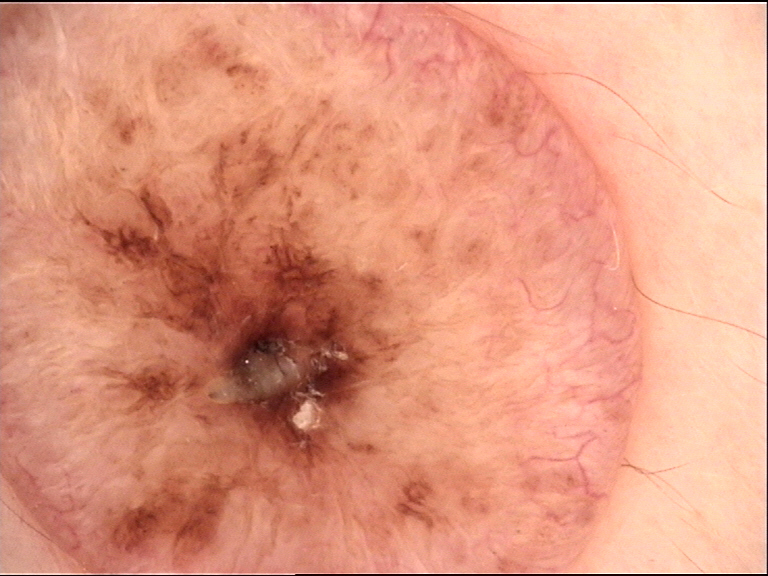modality = dermatoscopy; diagnosis = dermal nevus (expert consensus).